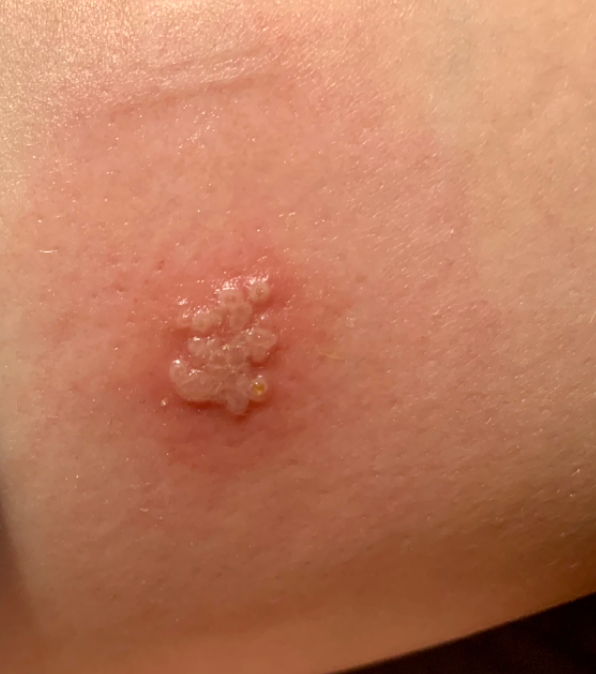{"duration": "less than one week", "systemic_symptoms": "none reported", "shot_type": "close-up", "symptoms": ["enlargement", "itching", "bothersome appearance", "pain", "burning"], "patient": "female, age 30–39", "body_site": "leg", "texture": "fluid-filled", "differential": {"leading": ["Herpes Simplex"]}}